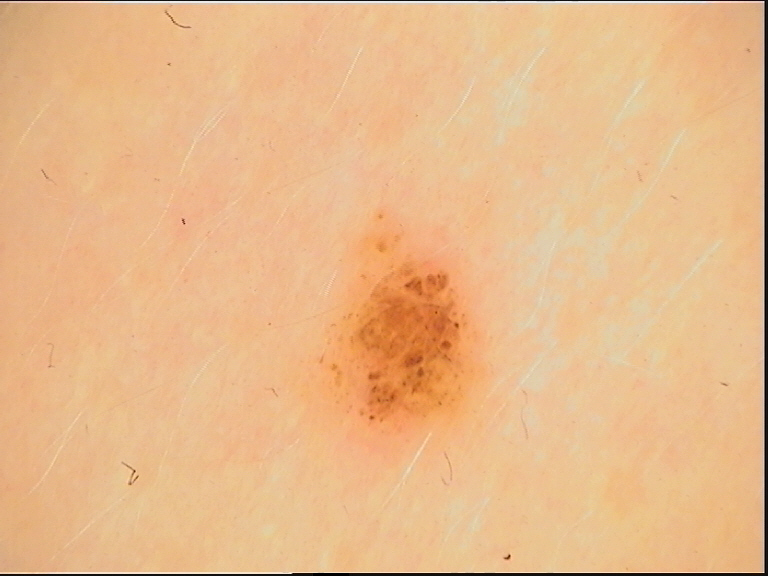Impression: The diagnostic label was a junctional nevus.